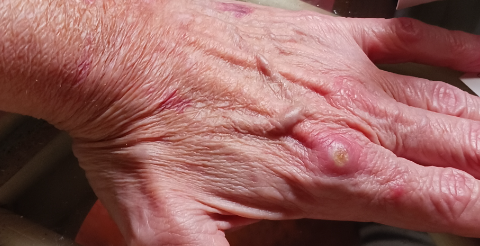This image was taken at a distance. On remote dermatologist review, most likely SCC/SCCIS; also consider Abscess; an alternative is Cyst.